A dermoscopic photograph of a skin lesion.
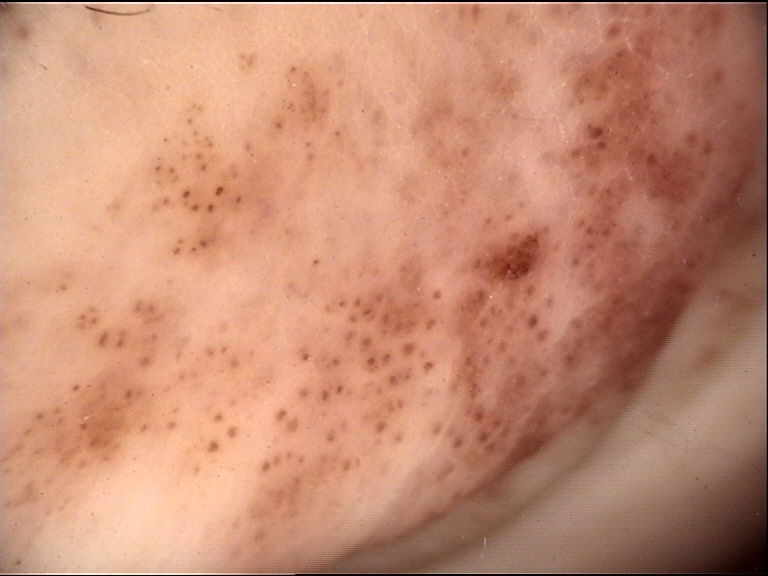Labeled as a banal lesion — a congenital compound nevus.